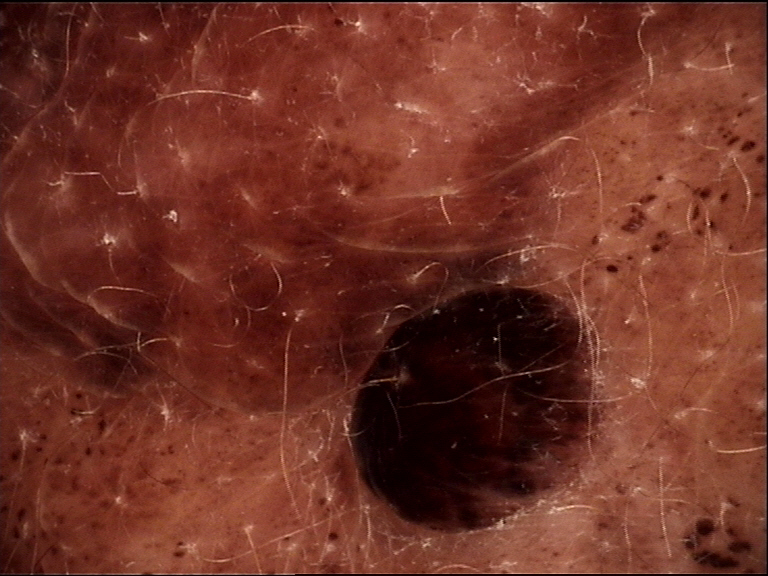Diagnosed as a banal lesion — a congenital compound nevus.